Recorded as Fitzpatrick II; a male patient roughly 50 years of age; dermoscopy of a skin lesion: 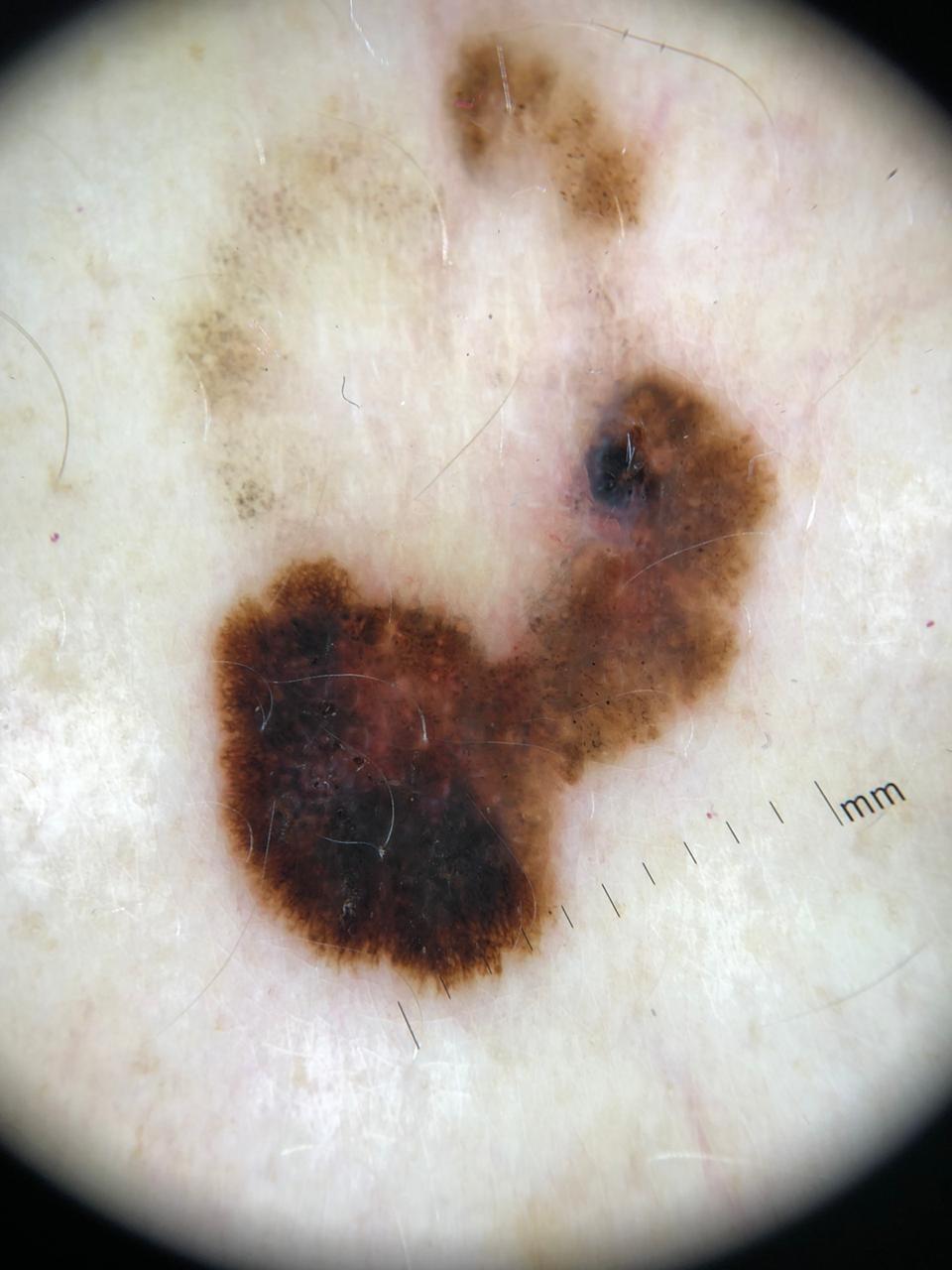Case:
* location: the trunk, specifically the anterior trunk
* diagnostic label: Melanoma (biopsy-proven)